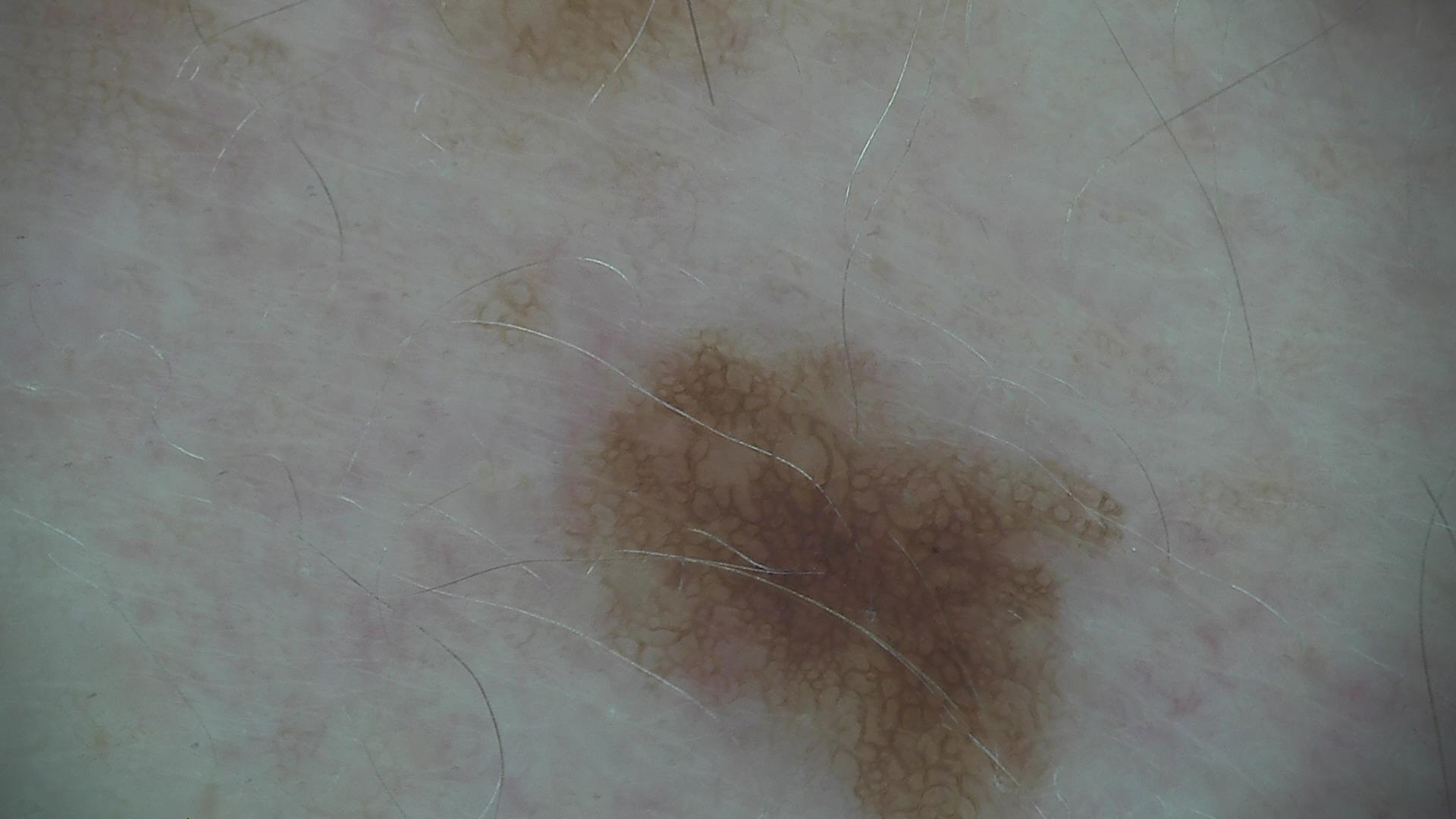Findings:
* imaging — dermatoscopy
* diagnostic label — dysplastic junctional nevus (expert consensus)